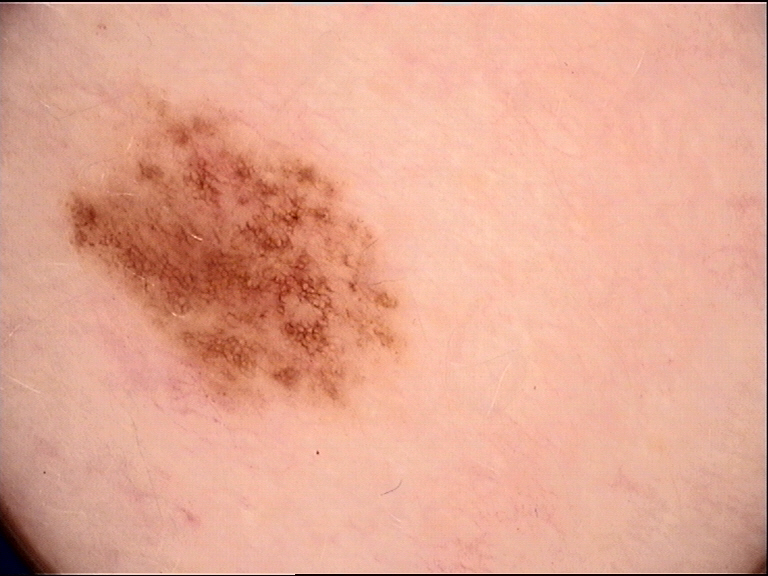Impression: The diagnosis was a benign lesion — a dysplastic junctional nevus.